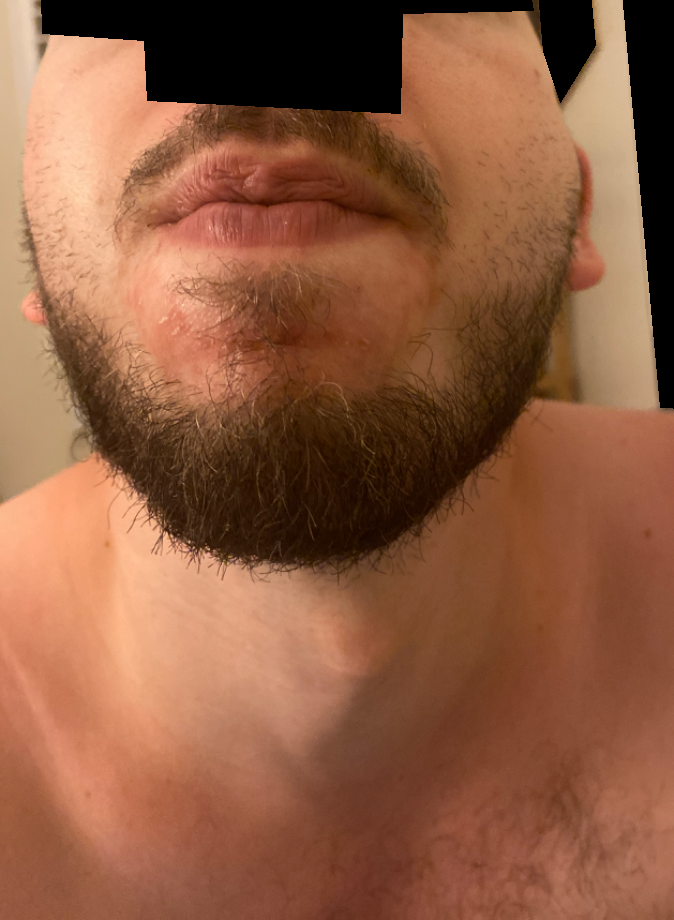  differential:
    leading:
      - Seborrheic Dermatitis
    considered:
      - Impetigo
      - Psoriasis